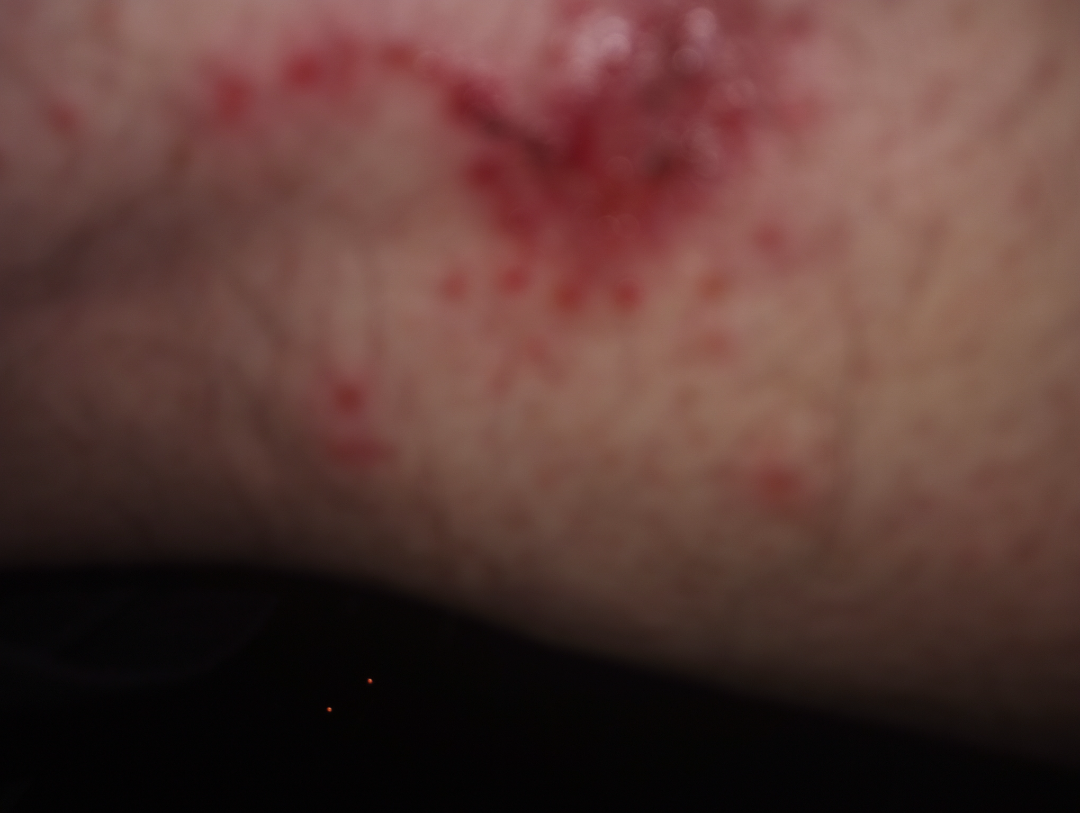Notes:
* subject · male, age 60–69
* anatomic site · leg
* surface texture · raised or bumpy and rough or flaky
* shot type · at an angle
* assessment · Impetigo and Herpes Zoster were considered with similar weight; lower on the differential is Infected eczema